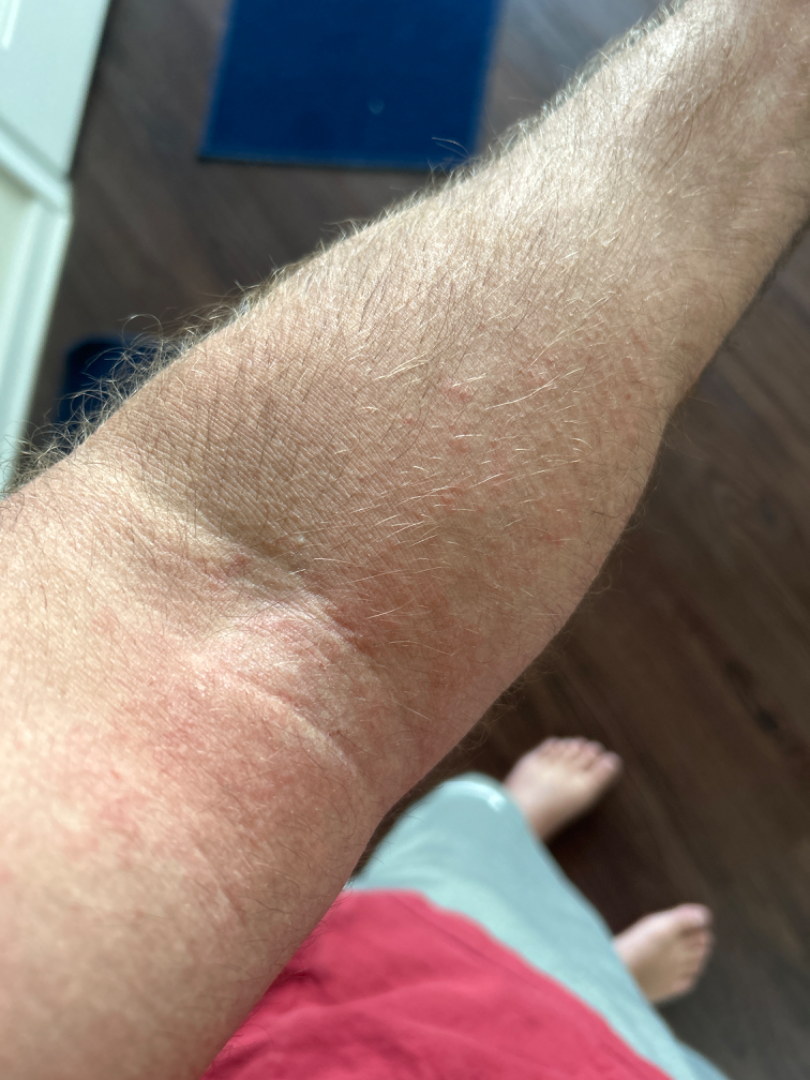One reviewing dermatologist: the leading consideration is Eczema; also consider Contact dermatitis, NOS; lower on the differential is Viral Exanthem.